Fitzpatrick phototype II · no associated lesion symptoms were reported · the arm is involved · self-categorized by the patient as a rash · the photo was captured at an angle · the patient reported no systemic symptoms · present for about one day · the contributor notes the lesion is raised or bumpy · the patient is 60–69, female: 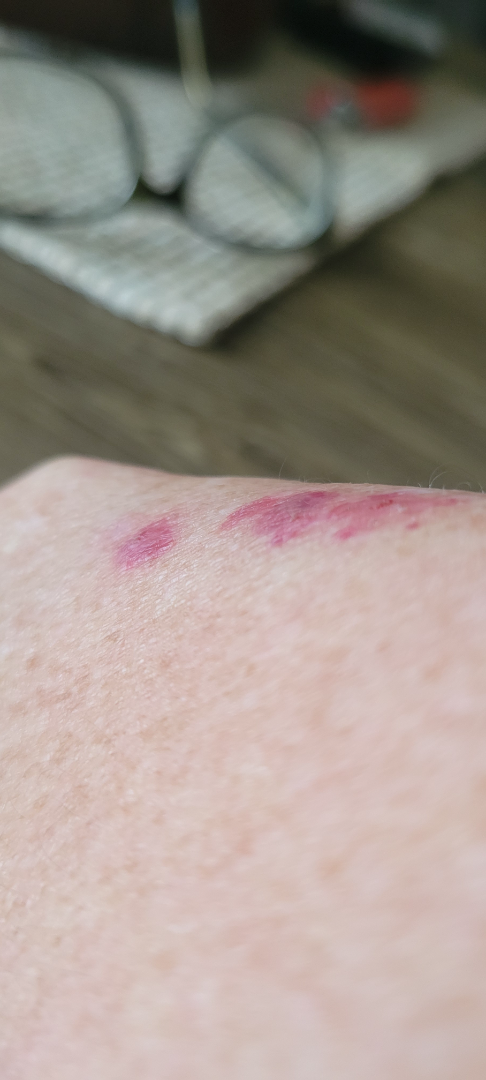Assessment: The differential is split between Abrasion, scrape, or scab and Allergic Contact Dermatitis.